Per the chart, a previous melanoma; a male patient aged 78 to 82; recorded as Fitzpatrick skin type II; a clinical photograph showing a skin lesion in context.
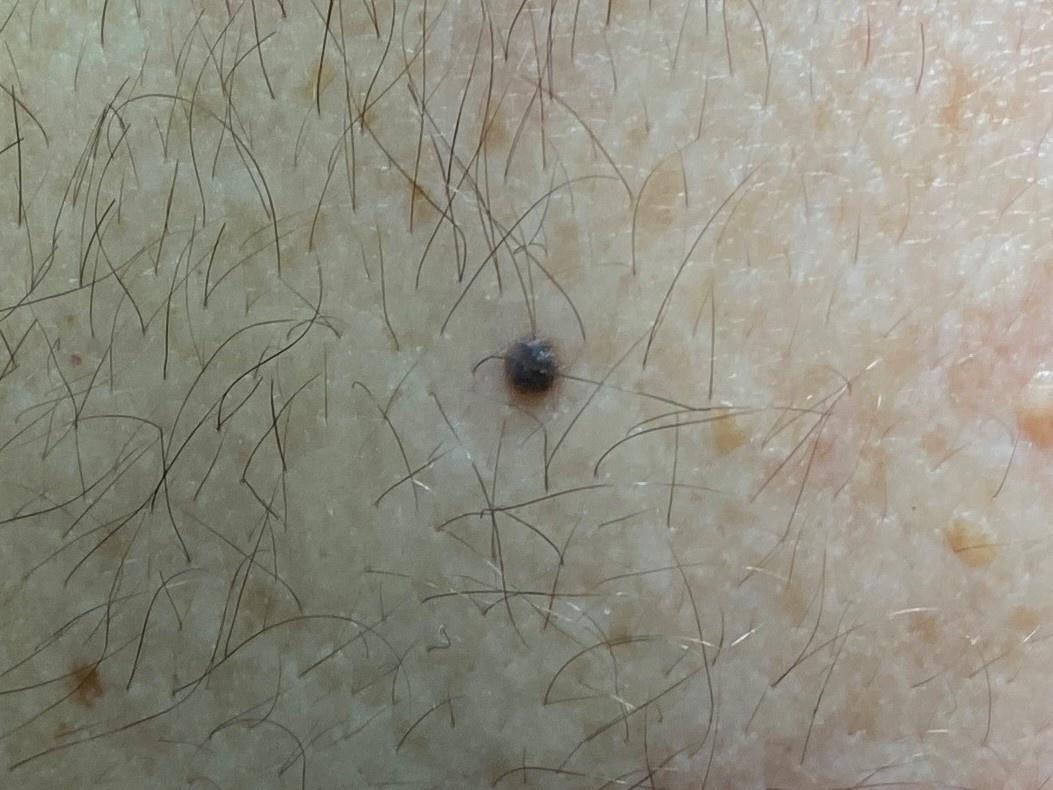The lesion involves the trunk, specifically the anterior trunk.
Histopathological examination showed a benign lesion — a nevus.